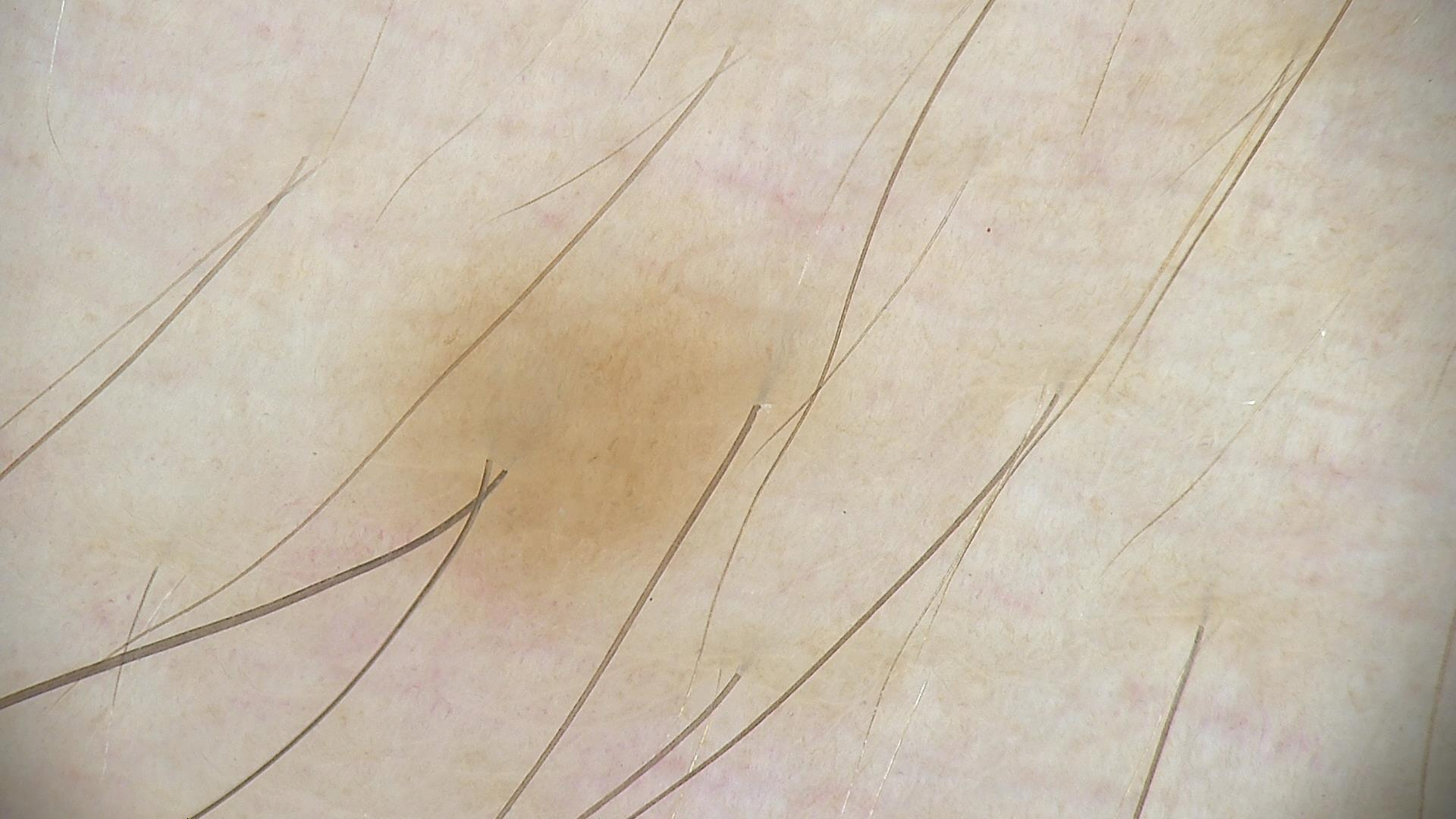<dermoscopy>
  <image>dermatoscopy</image>
  <diagnosis>
    <name>dysplastic junctional nevus</name>
    <code>jd</code>
    <malignancy>benign</malignancy>
    <super_class>melanocytic</super_class>
    <confirmation>expert consensus</confirmation>
  </diagnosis>
</dermoscopy>